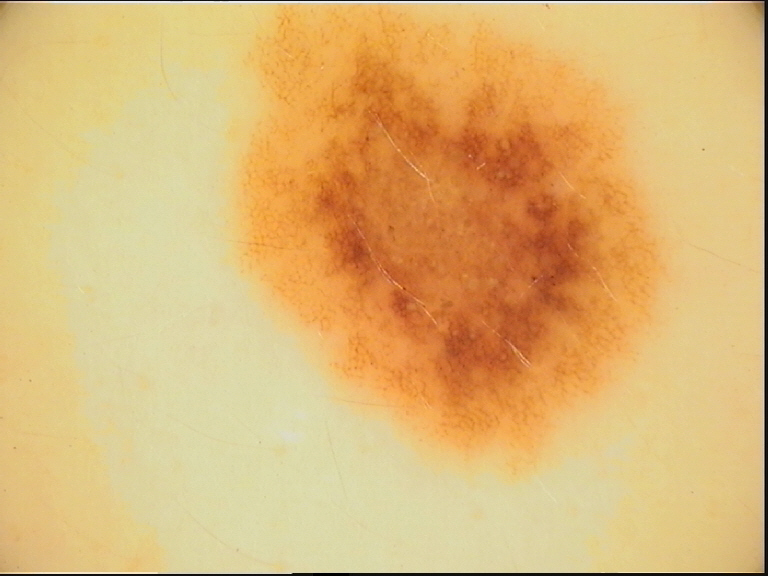assessment=dysplastic junctional nevus (expert consensus).